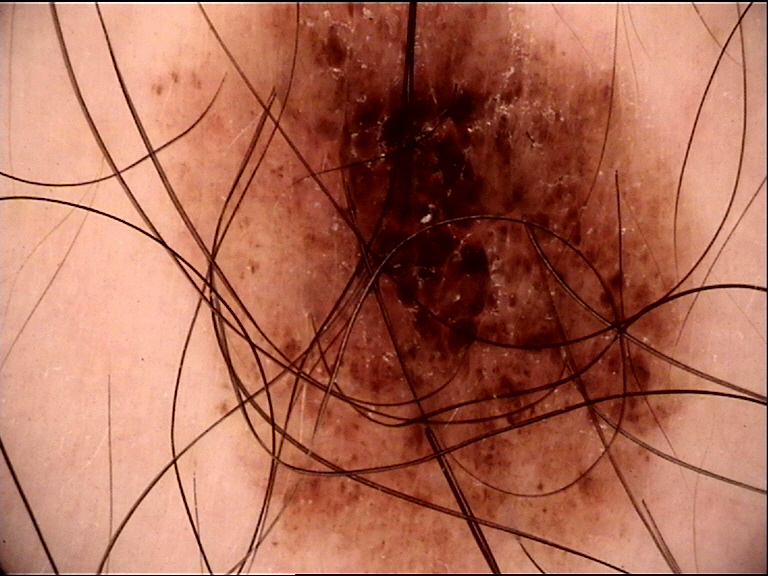A dermatoscopic image of a skin lesion.
This is a banal lesion.
Diagnosed as a compound nevus.